A dermoscopic image of a skin lesion; the patient says their skin tans without first burning; few moles overall by the patient's own estimate; a female subject 67 years of age — 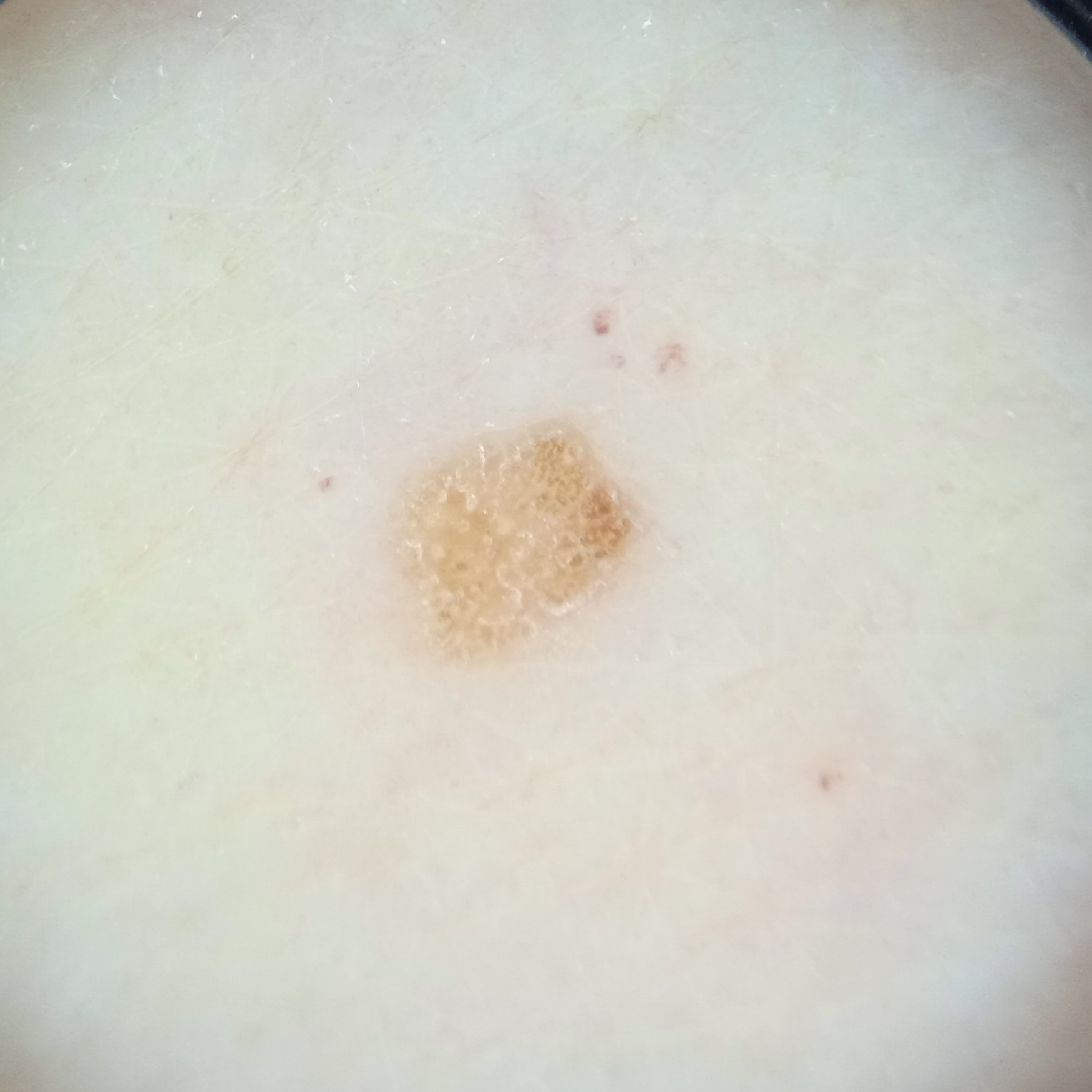{"lesion_location": "an arm", "diagnosis": {"name": "seborrheic keratosis", "malignancy": "benign"}}